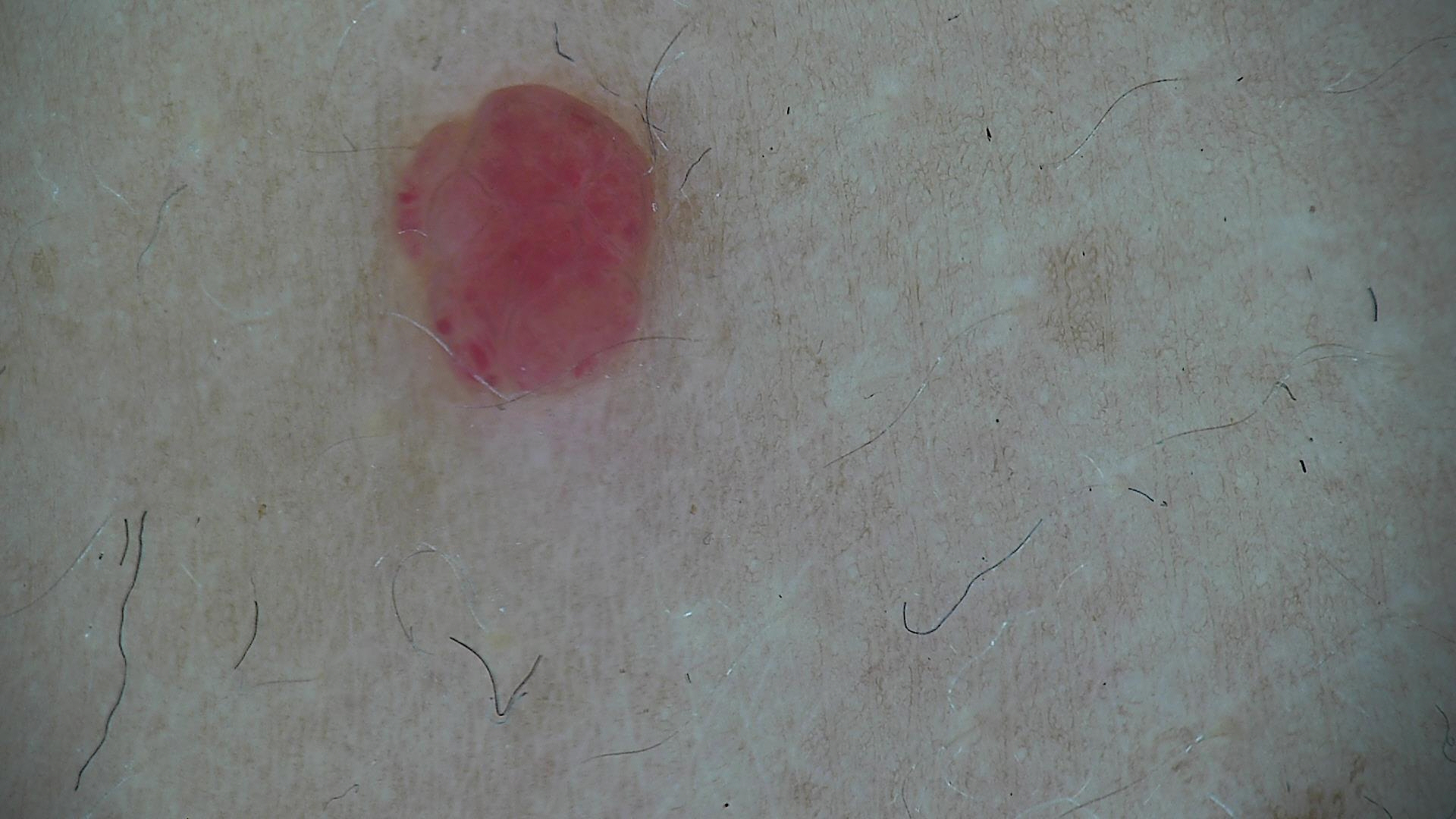Findings:
* diagnostic label — hemangioma (expert consensus)